A close-up photograph. Texture is reported as raised or bumpy. The contributor is 30–39, female. The patient indicates itching, enlargement and bothersome appearance. No relevant systemic symptoms. Self-categorized by the patient as a rash. The patient indicates the condition has been present for less than one week — 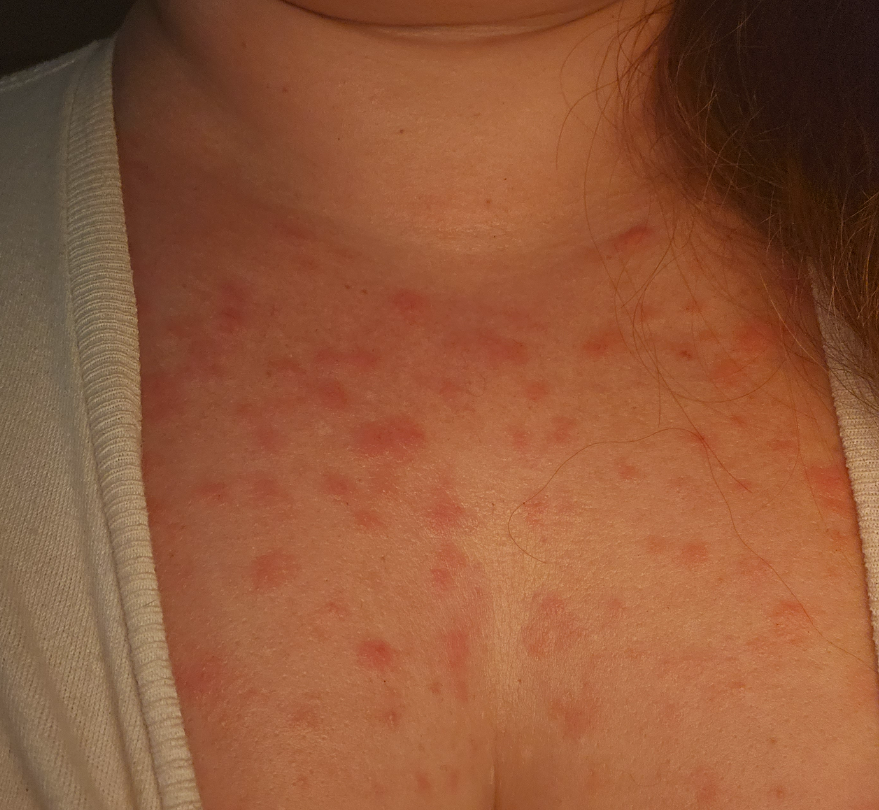Findings:
• assessment: ungradable on photographic review